The lesion involves the front of the torso; male contributor, age 18–29; the photograph is a close-up of the affected area:
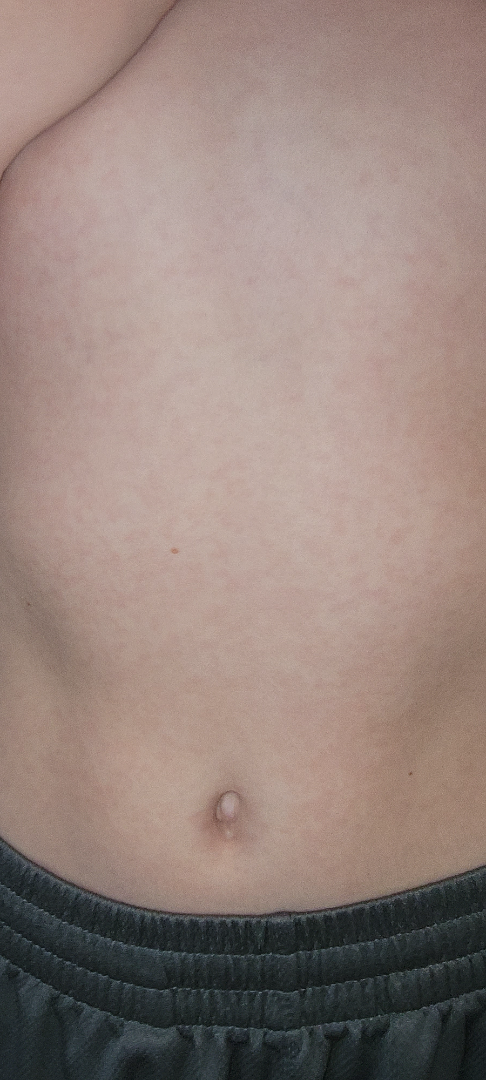No discernible skin pathology was identified on dermatologist review.
Texture is reported as flat.
The patient described the issue as a rash.
The patient did not report lesion symptoms.
No constitutional symptoms were reported.
The contributor notes the condition has been present for about one day.